A dermatoscopic image of a skin lesion.
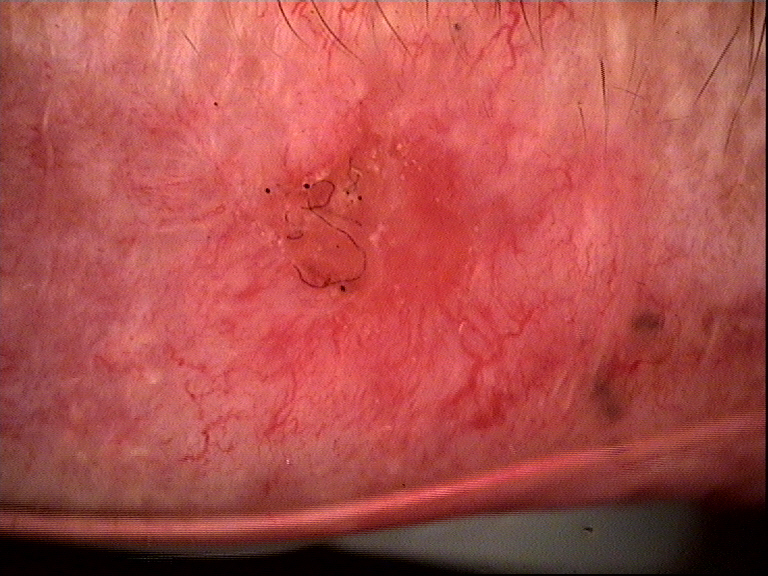Histopathologically confirmed as a keratinocytic, malignant lesion — a basal cell carcinoma.